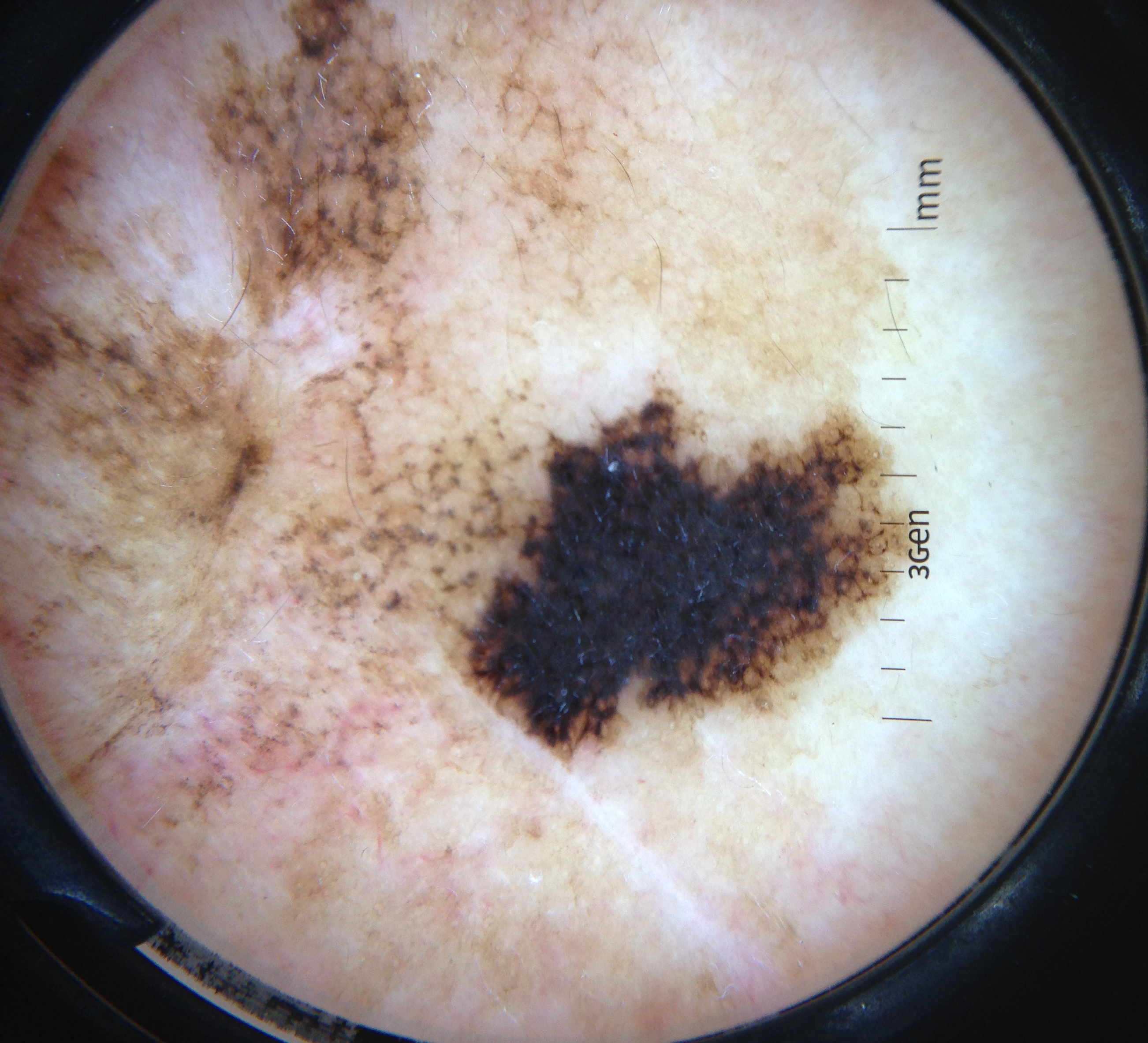Conclusion:
Histopathology confirmed a skin cancer — a lentigo maligna.